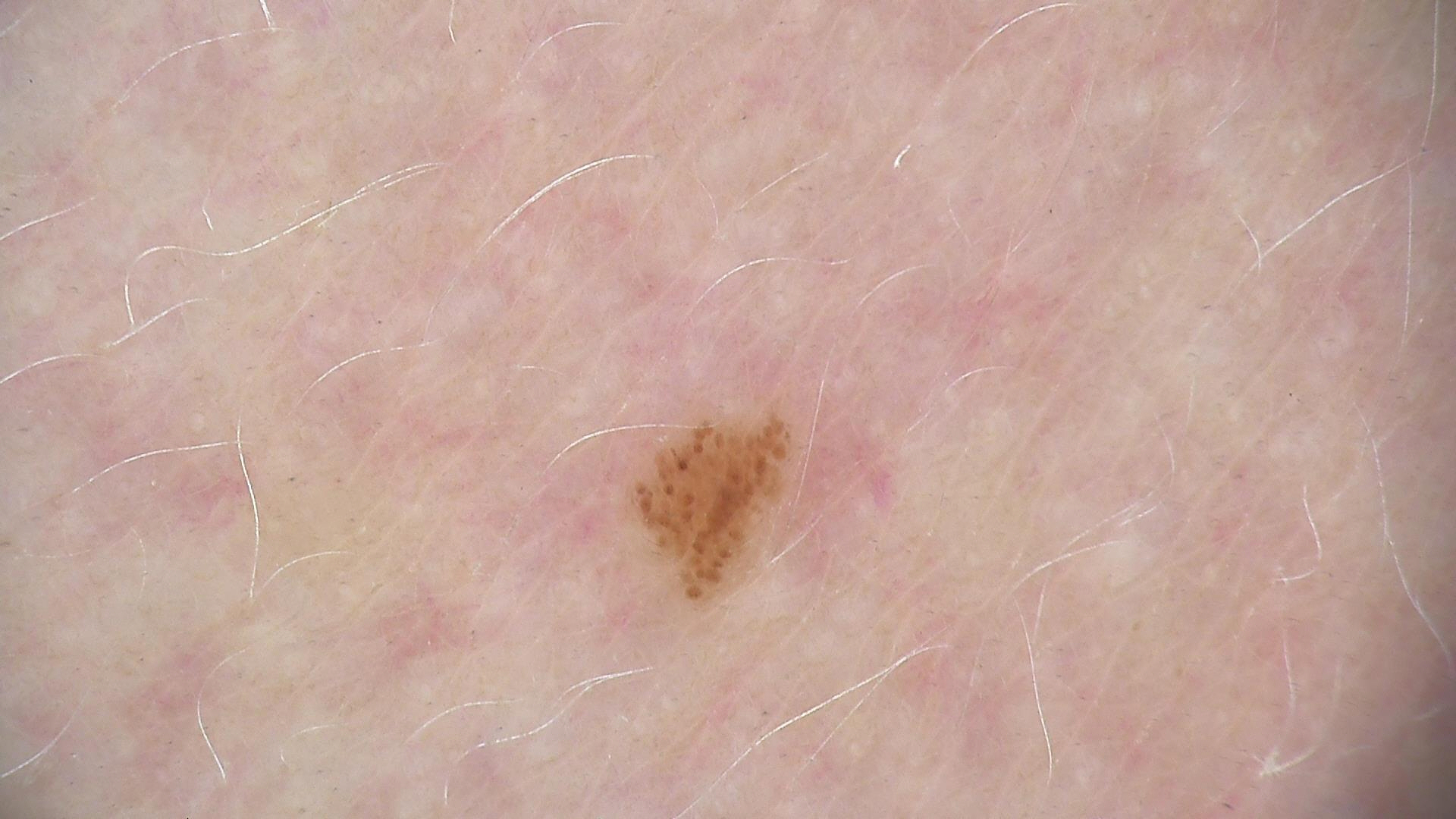  image: dermoscopy
  diagnosis:
    name: dysplastic junctional nevus
    code: jd
    malignancy: benign
    super_class: melanocytic
    confirmation: expert consensus